A clinical close-up photograph of a skin lesion · a subject 65 years old.
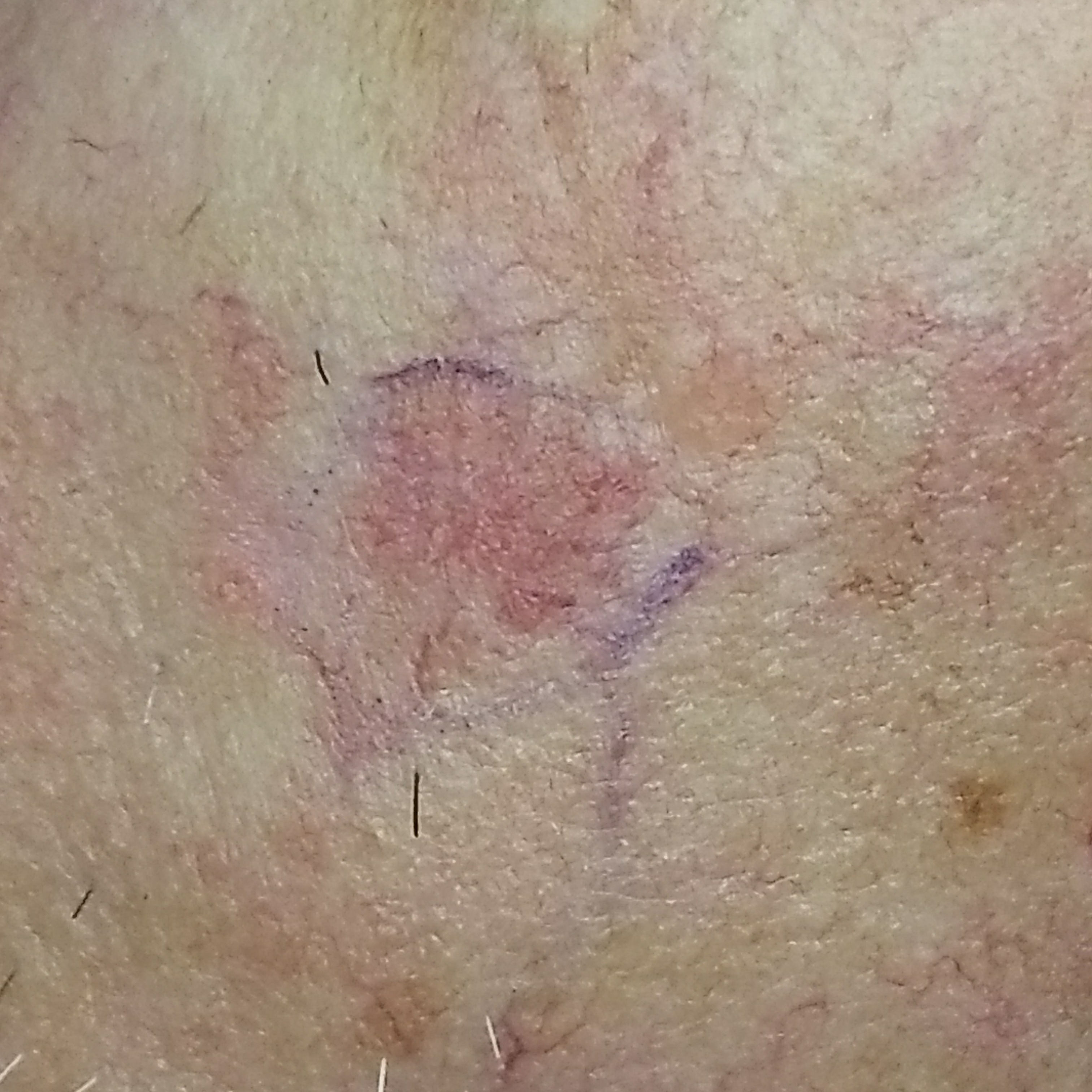The lesion was found on the face.
By the patient's account, the lesion has bled and itches, but has not changed.
The diagnostic impression was an actinic keratosis.